The photo was captured at a distance — 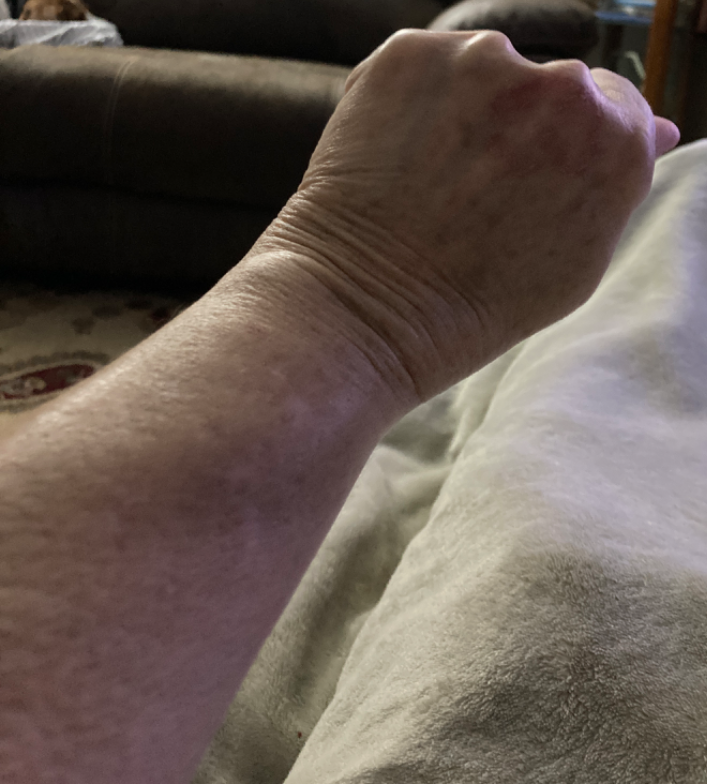• clinical impression: Tinea and Eczema were considered with similar weight; less probable is Psoriasis